The patient was assessed as Fitzpatrick skin type II; a male patient age 58; a clinical photo of a skin lesion taken with a smartphone:
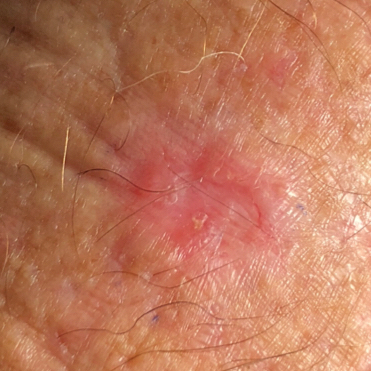lesion_size:
  diameter_1_mm: 15.0
  diameter_2_mm: 12.0
symptoms:
  present:
    - growth
    - change in appearance
    - itching
    - elevation
  absent:
    - bleeding
diagnosis:
  name: basal cell carcinoma
  code: BCC
  malignancy: malignant
  confirmation: histopathology